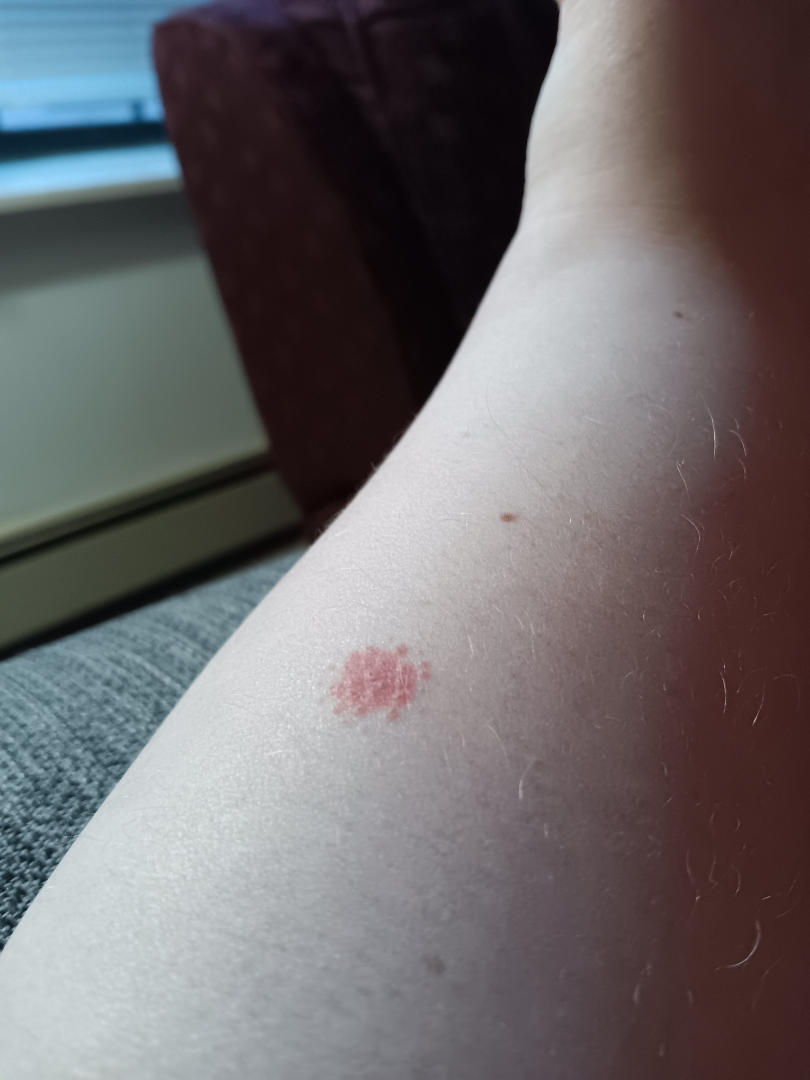Q: How does the lesion feel?
A: raised or bumpy
Q: Image view?
A: at an angle
Q: Reported symptoms?
A: bothersome appearance and itching
Q: What is the affected area?
A: arm
Q: Who is the patient?
A: female, age 30–39
Q: How does the patient describe it?
A: a rash
Q: Duration?
A: one to four weeks
Q: What conditions are considered?
A: Acute dermatitis, NOS (possible); Acute and chronic dermatitis (possible)